Collected as part of a research study, without a referral diagnosis · the patient says their skin reddens painfully with sun exposure · a female subject aged 81.
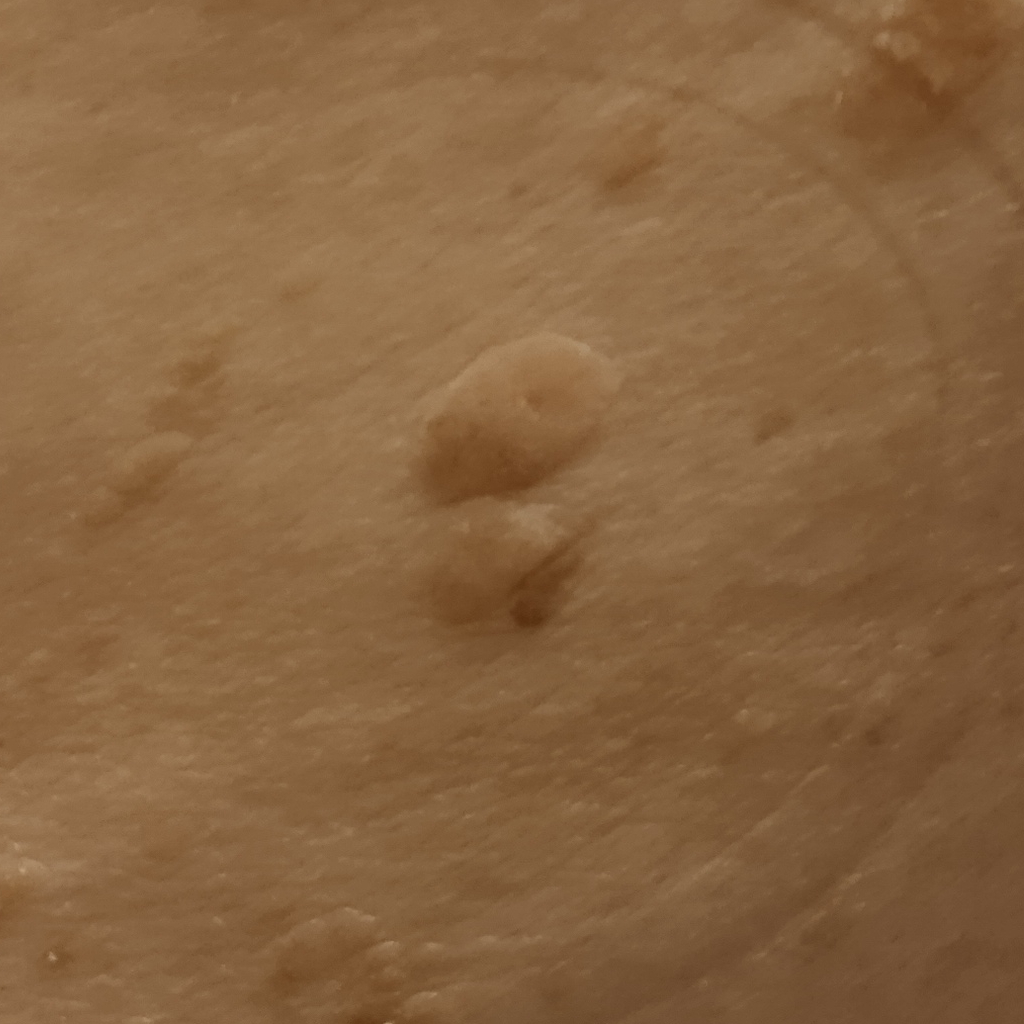Q: Where is the lesion?
A: the back
Q: How large is the lesion?
A: 15.5 mm
Q: What was the diagnosis?
A: seborrheic keratosis (dermatologist consensus)